An image taken at an angle — 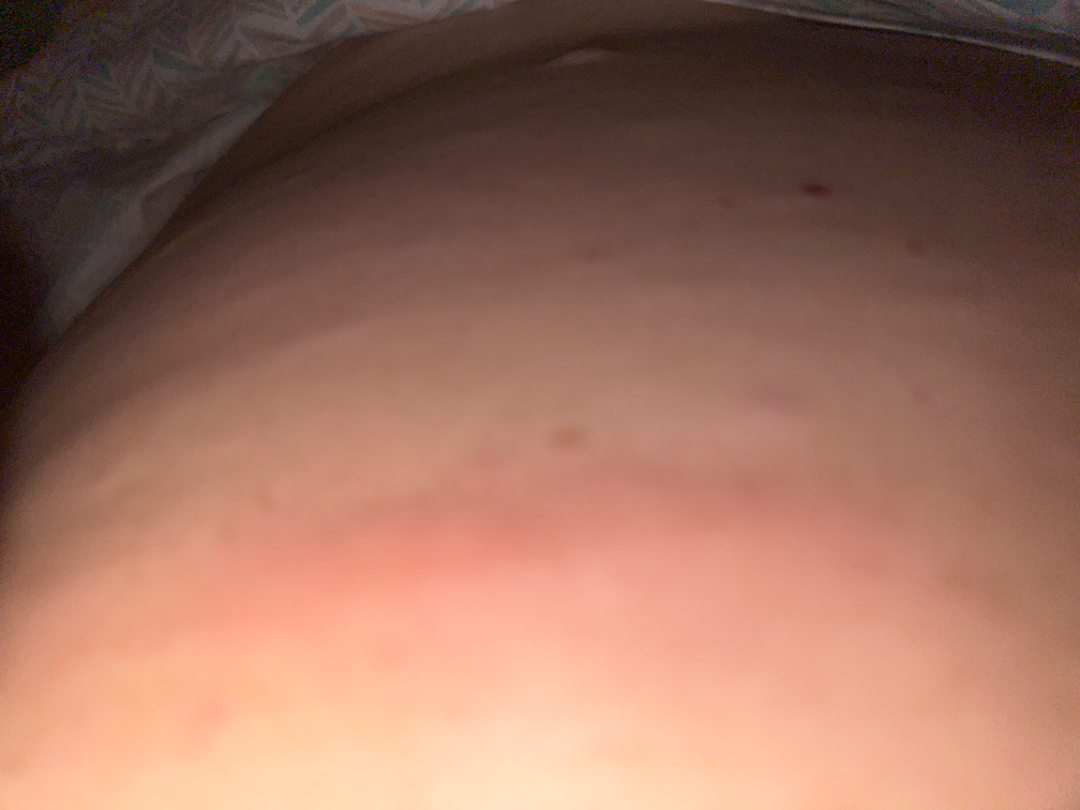FST III; lay graders estimated Monk Skin Tone 2 or 3. One reviewing dermatologist: the impression was split between Abscess and Cellulitis.